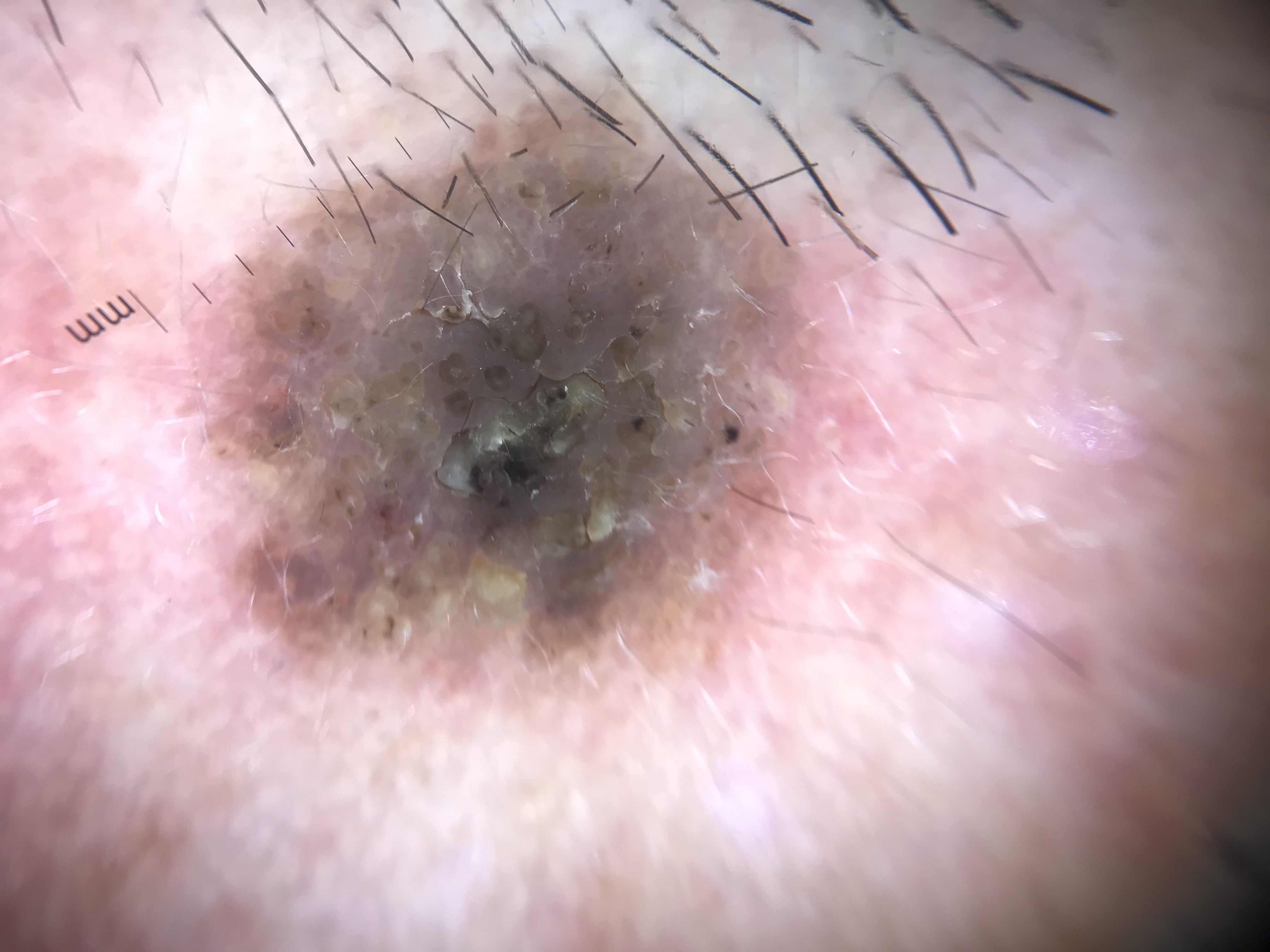Q: What was the diagnostic impression?
A: seborrheic keratosis (expert consensus)